The lesion involves the arm. This image was taken at an angle: 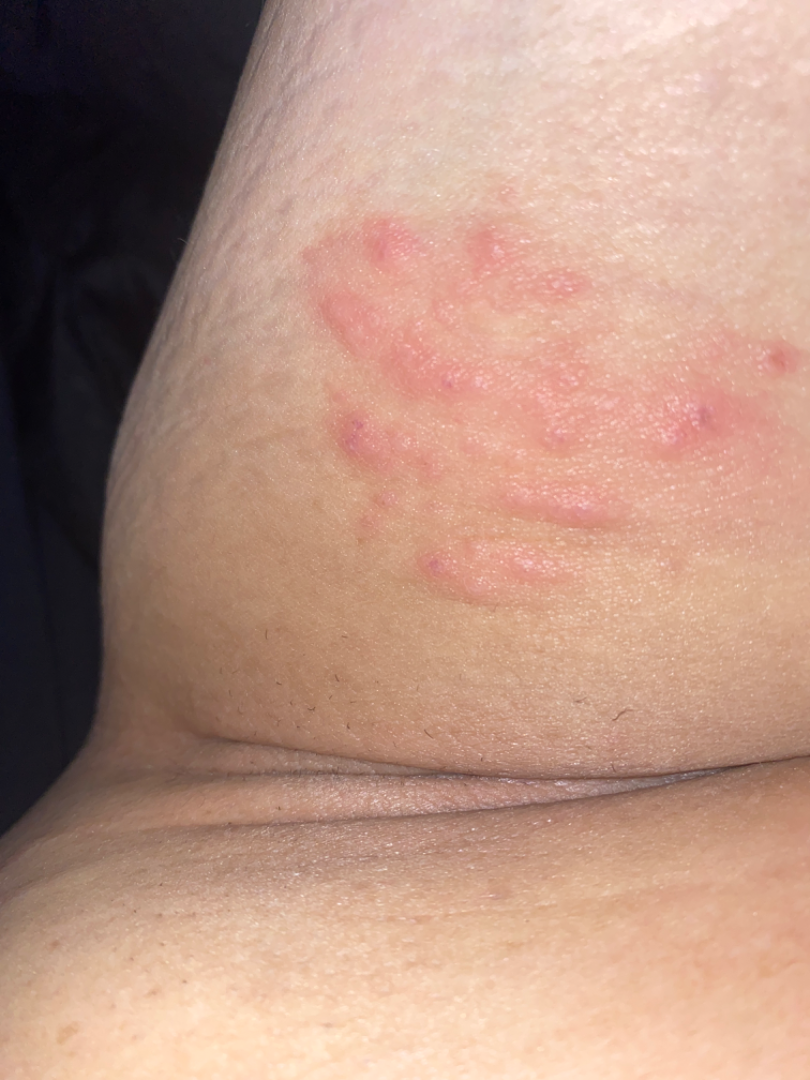| field | value |
|---|---|
| assessment | indeterminate from the photograph |